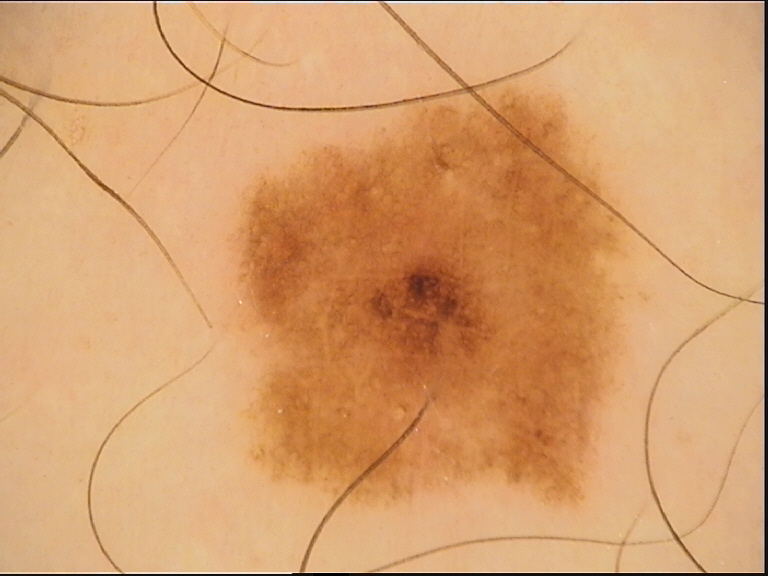Diagnosed as a dysplastic junctional nevus.